The affected area is the back of the hand and head or neck · female subject, age 70–79 · this image was taken at an angle.
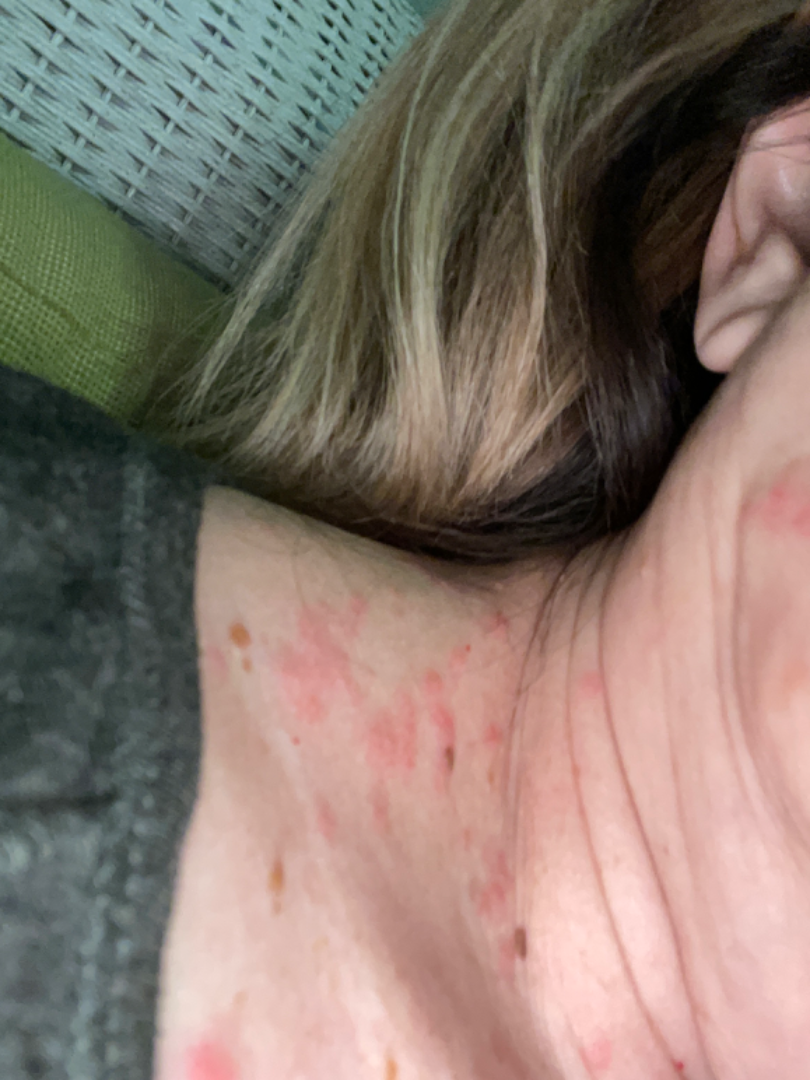{"assessment": "ungradable on photographic review"}